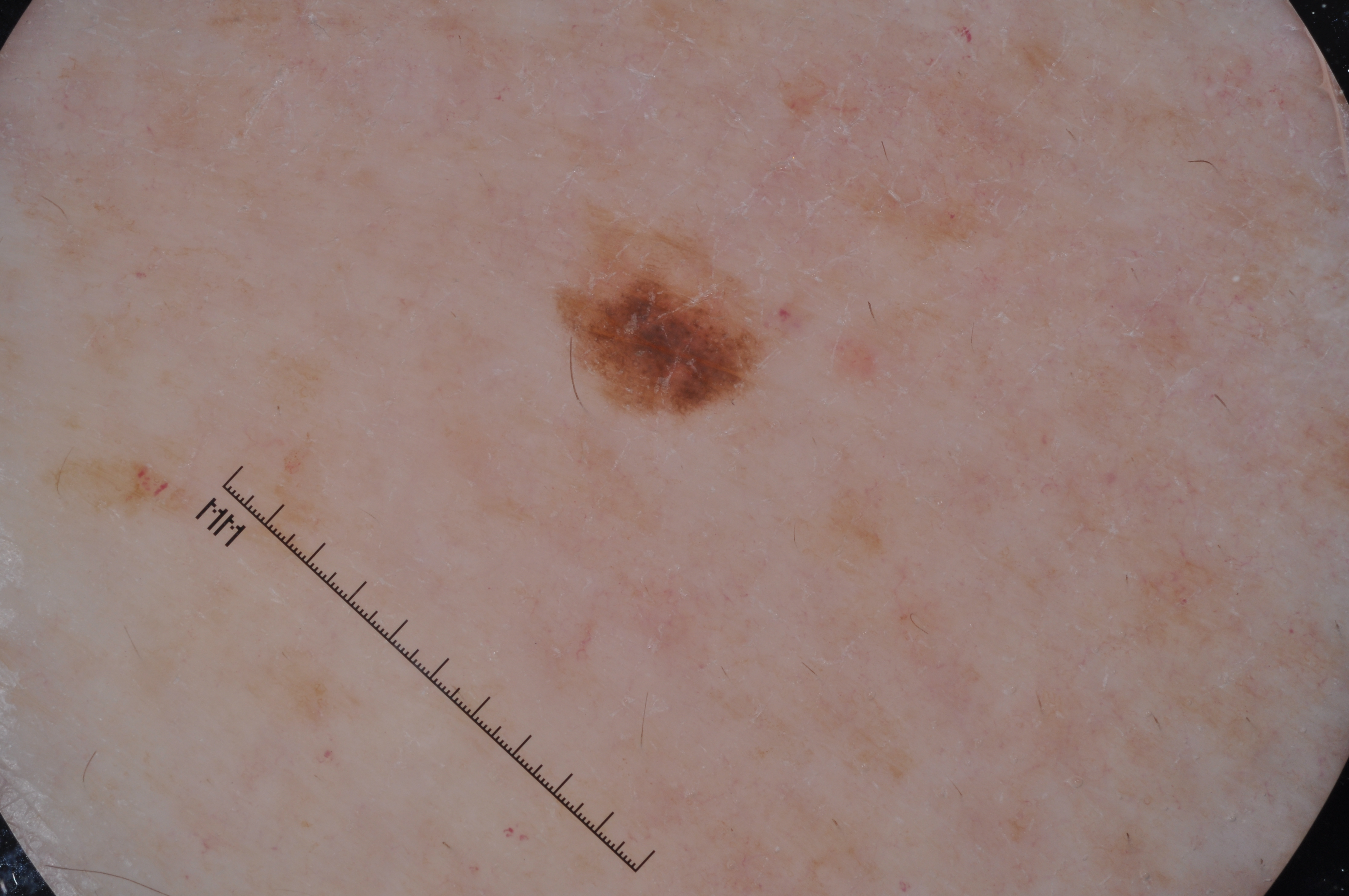Findings:
A dermatoscopic image of a skin lesion. A female patient, roughly 65 years of age. Dermoscopically, the lesion shows pigment network and milia-like cysts; no streaks or negative network. The visible lesion spans <box>569, 238, 759, 406</box>.
Pathology:
On biopsy, the diagnosis was a melanoma.